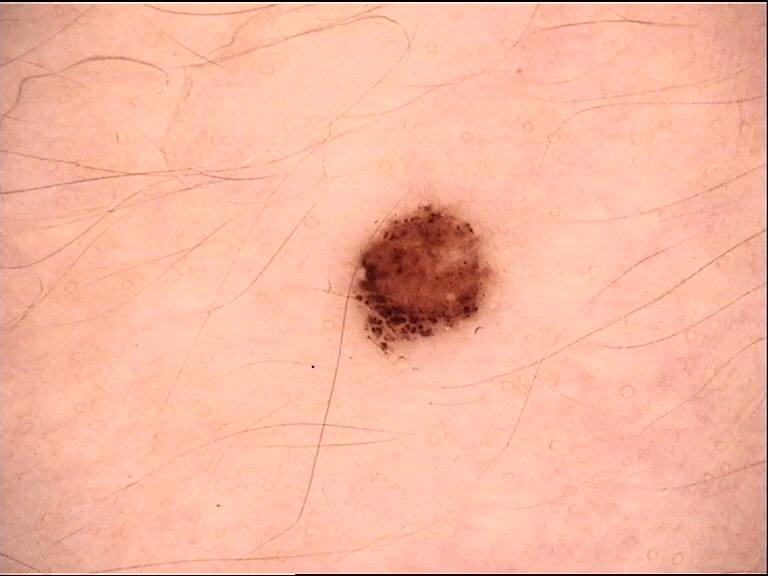A dermoscopy image of a single skin lesion. Consistent with a dysplastic junctional nevus.